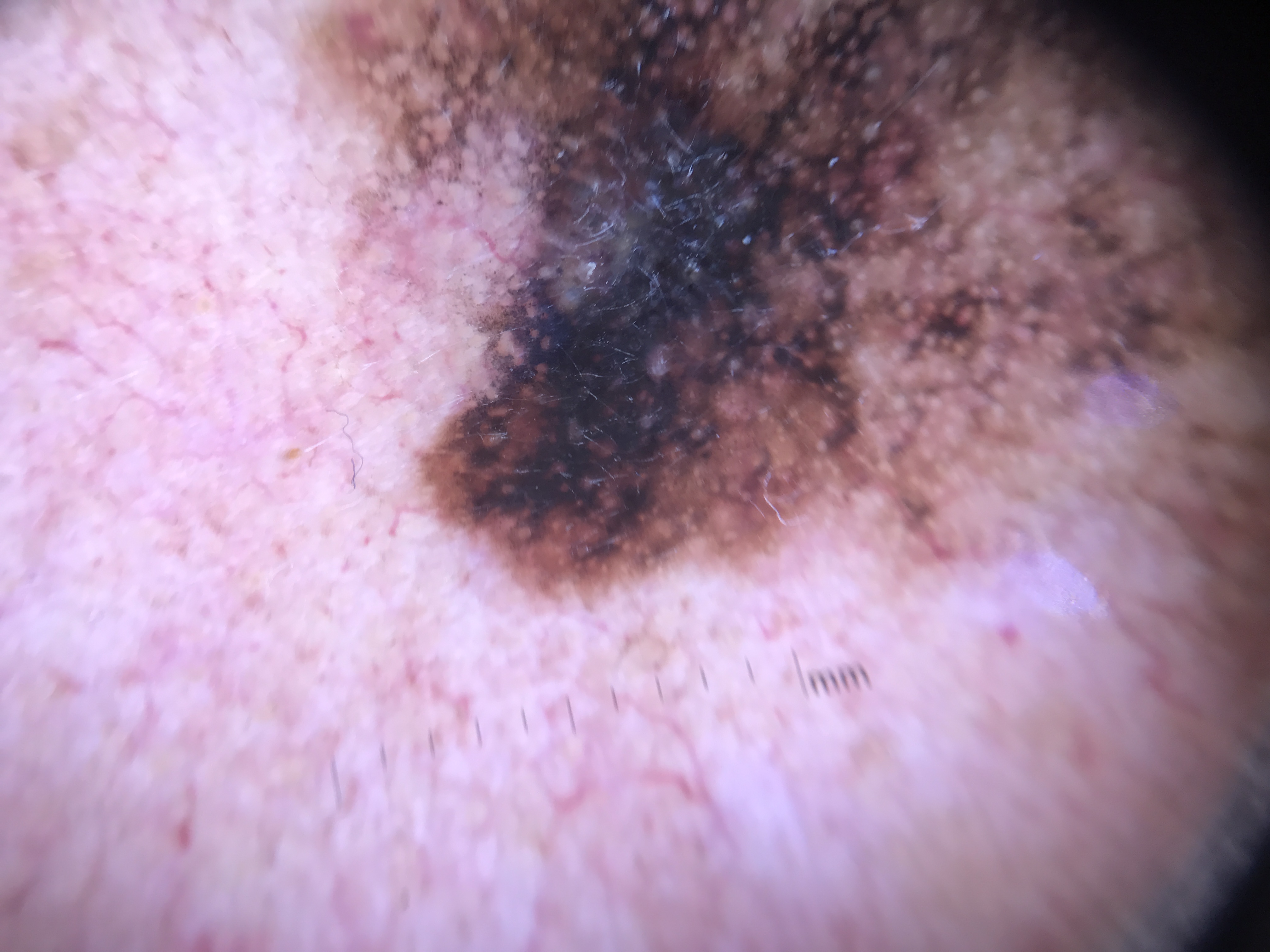image: dermatoscopy
diagnosis:
  name: lentigo maligna
  code: lm
  malignancy: malignant
  super_class: melanocytic
  confirmation: histopathology